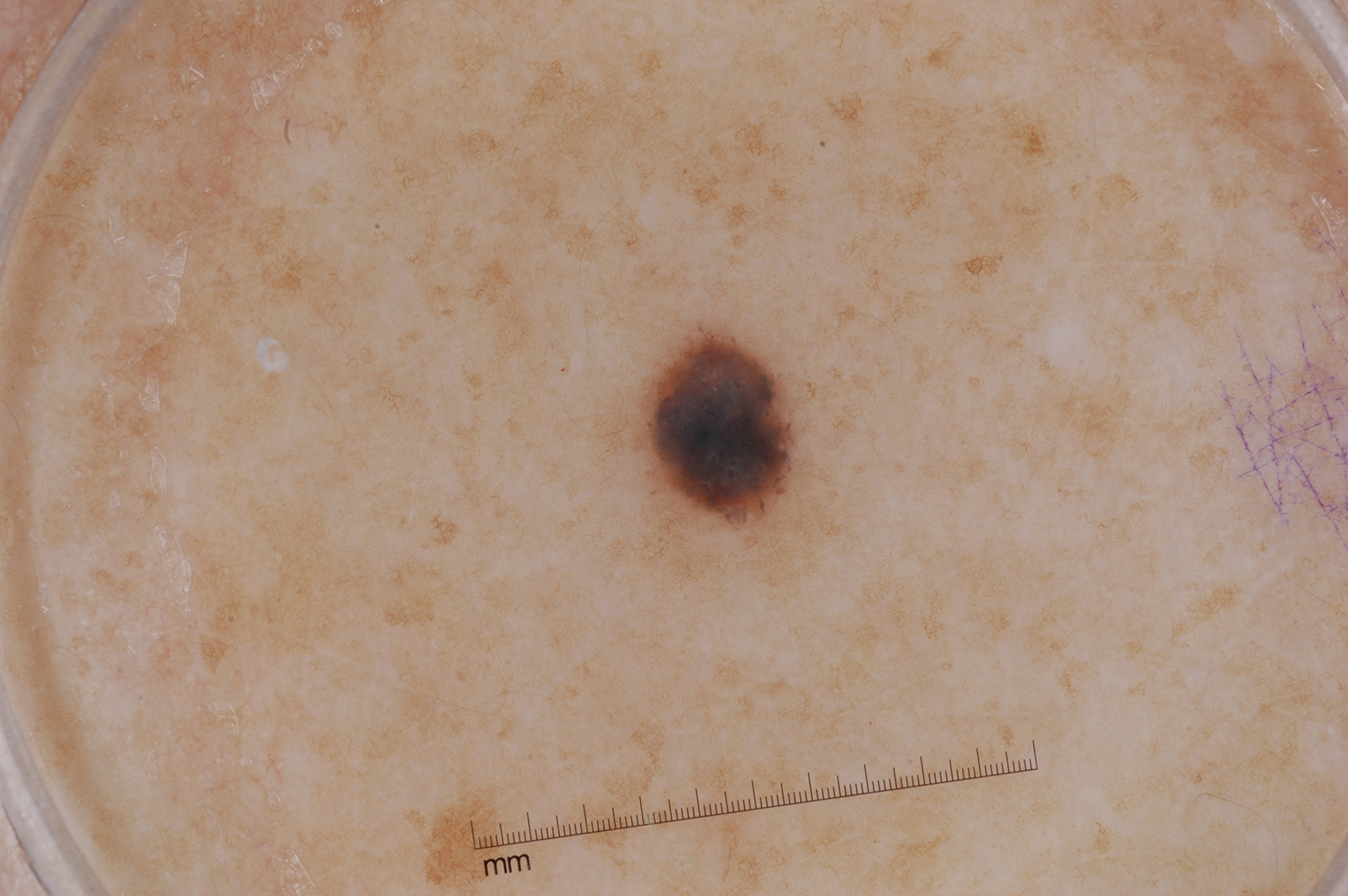{
  "image": {
    "modality": "dermoscopy"
  },
  "patient": {
    "sex": "female",
    "age_approx": 50
  },
  "lesion_location": {
    "bbox_xyxy": [
      639,
      322,
      797,
      530
    ]
  },
  "dermoscopic_features": {
    "present": [
      "milia-like cysts"
    ],
    "absent": [
      "pigment network",
      "streaks",
      "negative network"
    ]
  },
  "diagnosis": {
    "name": "melanocytic nevus",
    "malignancy": "benign",
    "lineage": "melanocytic",
    "provenance": "clinical"
  }
}